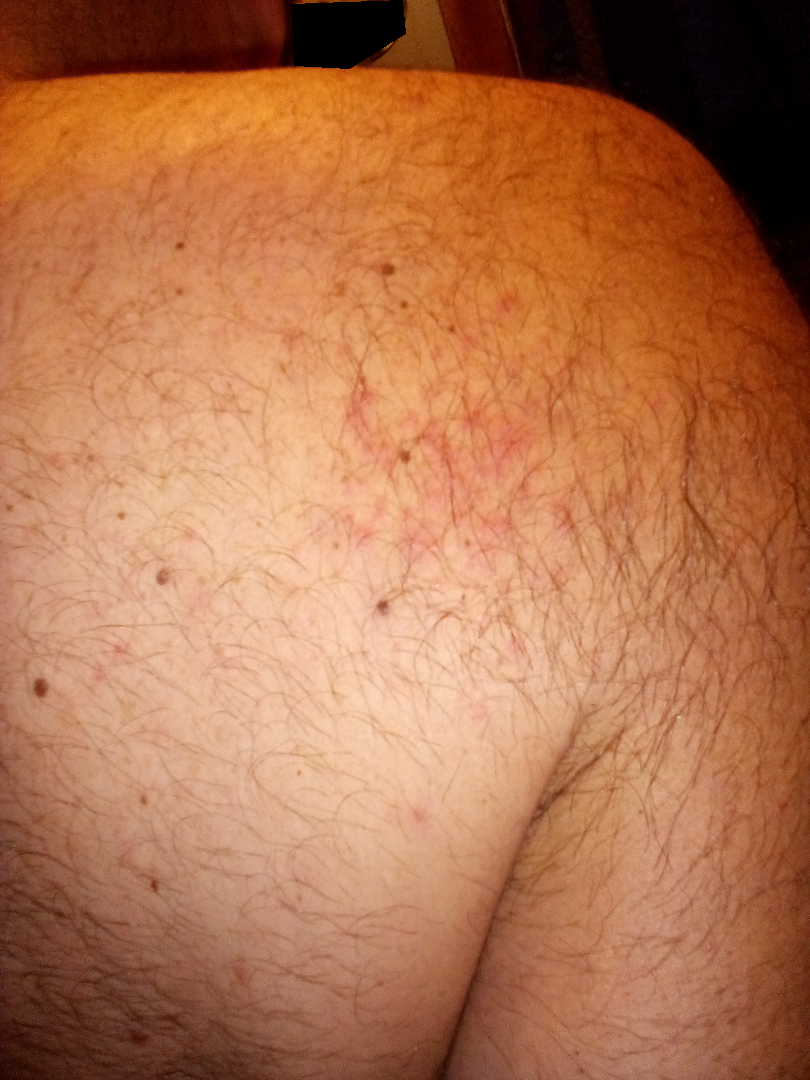Impression:
On photographic review by a dermatologist: the differential, in no particular order, includes Eczema and Allergic Contact Dermatitis.